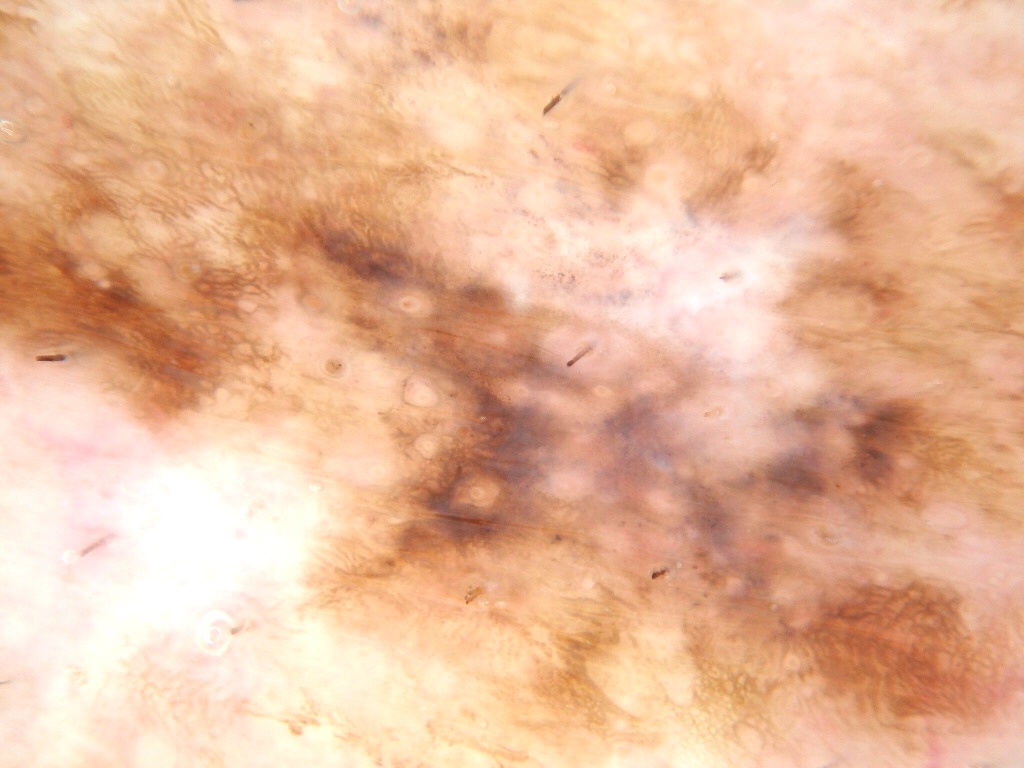Case summary:
• patient — male, roughly 85 years of age or older
• modality — dermatoscopic image of a skin lesion
• features — pigment network; absent: negative network, globules, milia-like cysts, and streaks
• field coverage — spans the dermoscopic field
• assessment — a melanoma, a malignancy